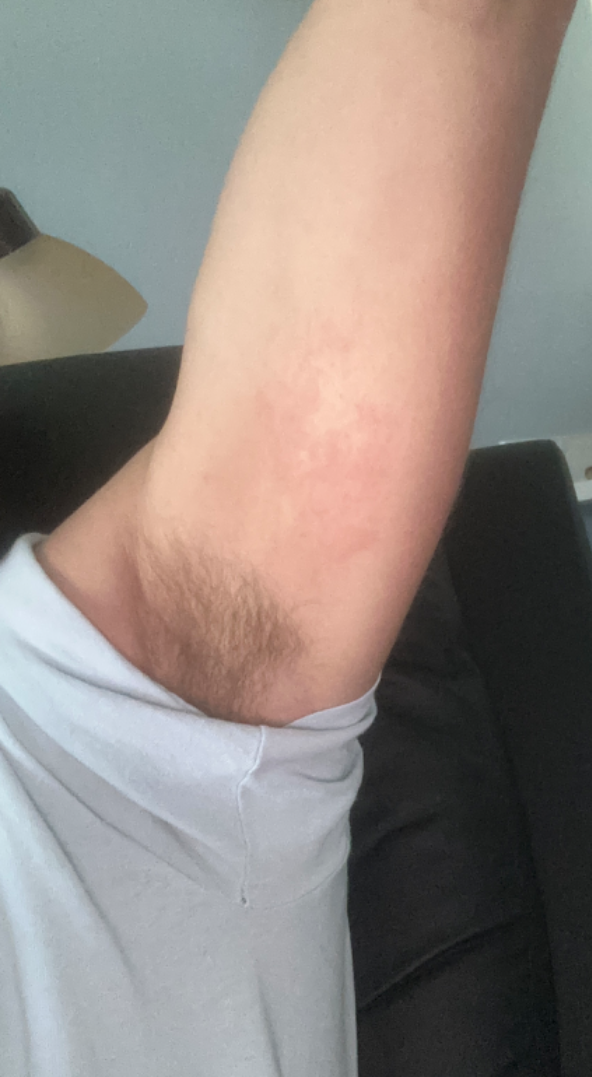{"assessment": "indeterminate from the photograph", "patient_category": "a rash", "symptoms": ["bothersome appearance", "itching", "burning"], "shot_type": "at a distance", "body_site": ["arm", "head or neck"], "texture": "flat"}